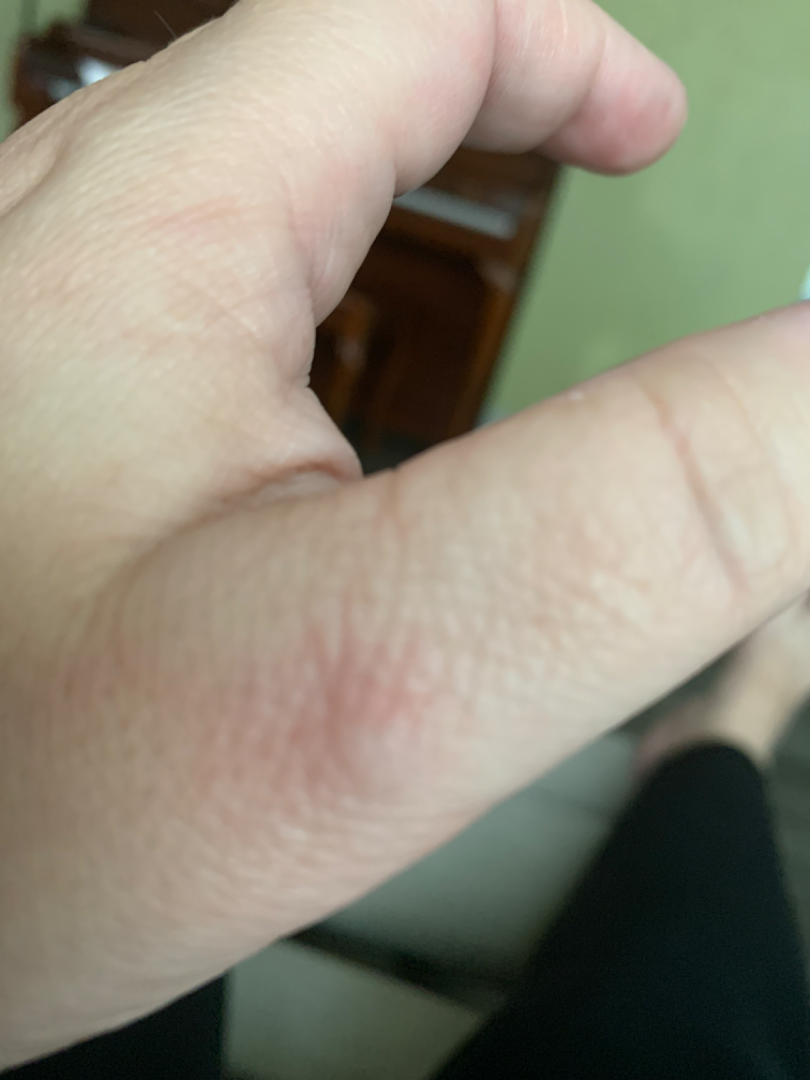assessment: ungradable on photographic review